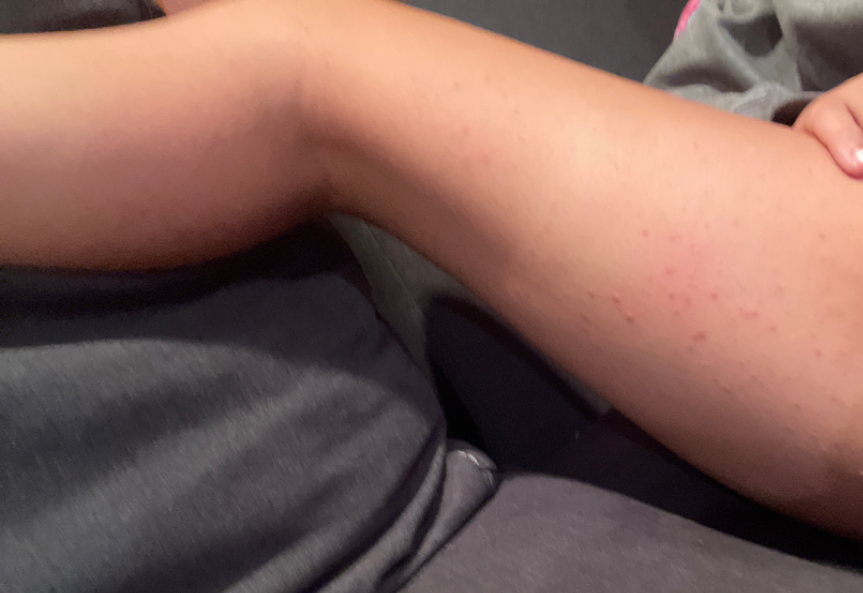The patient is 18–29, female.
This image was taken at a distance.
The reviewing clinician's impression was: most consistent with Folliculitis; also consider Keratosis pilaris; less probable is Eczema.